Self-categorized by the patient as a rash · the subject is female · this image was taken at a distance · located on the head or neck, front of the torso, arm, leg and back of the torso · the patient reported no systemic symptoms · the patient reports itching, darkening, bothersome appearance, pain, burning and enlargement · texture is reported as raised or bumpy · reported duration is one to three months — 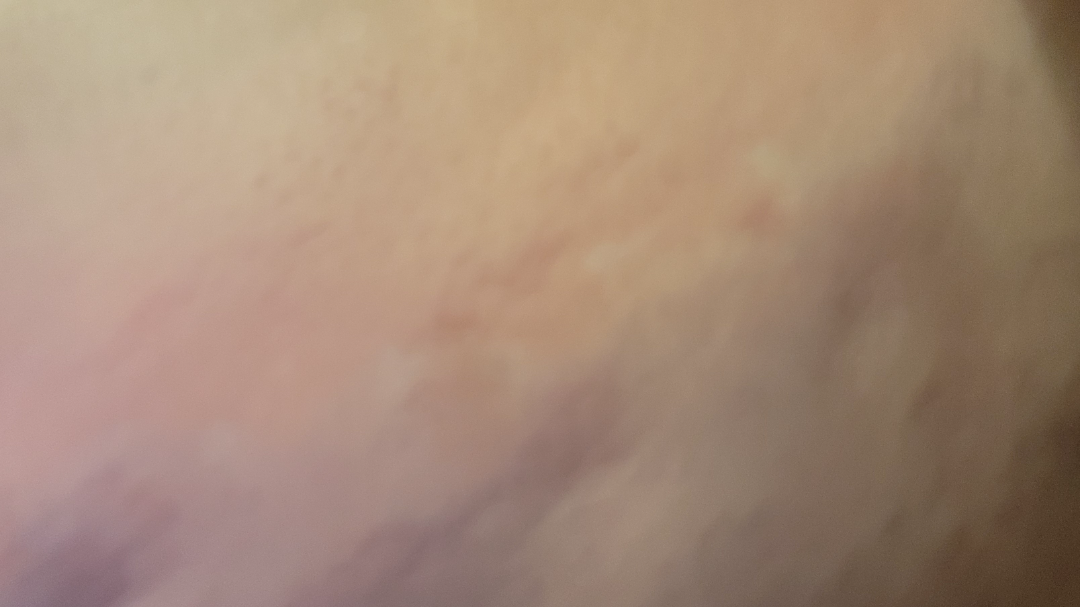Q: Could the case be diagnosed?
A: not assessable